This image was taken at a distance:
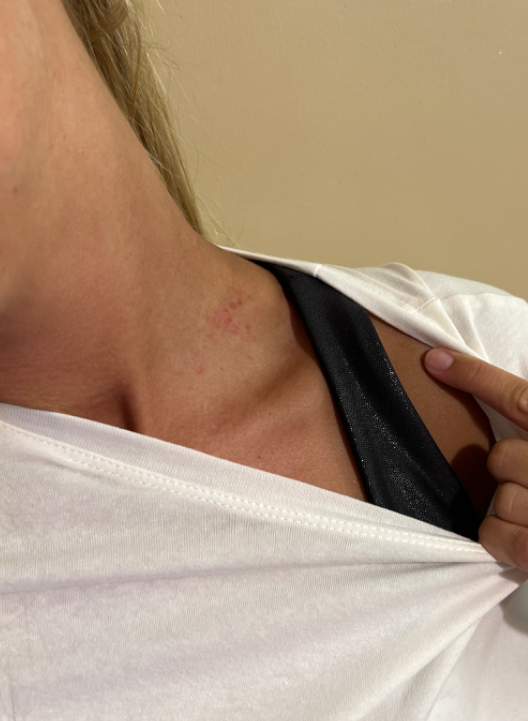clinical impression: consistent with Irritant Contact Dermatitis.